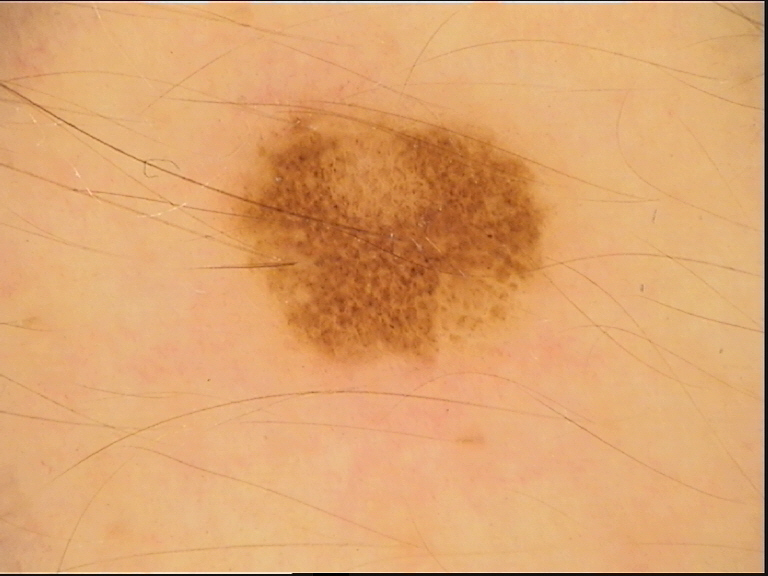{"image": "dermoscopy", "diagnosis": {"name": "dysplastic compound nevus", "code": "cd", "malignancy": "benign", "super_class": "melanocytic", "confirmation": "expert consensus"}}